The affected area is the back of the torso. This is a close-up image:
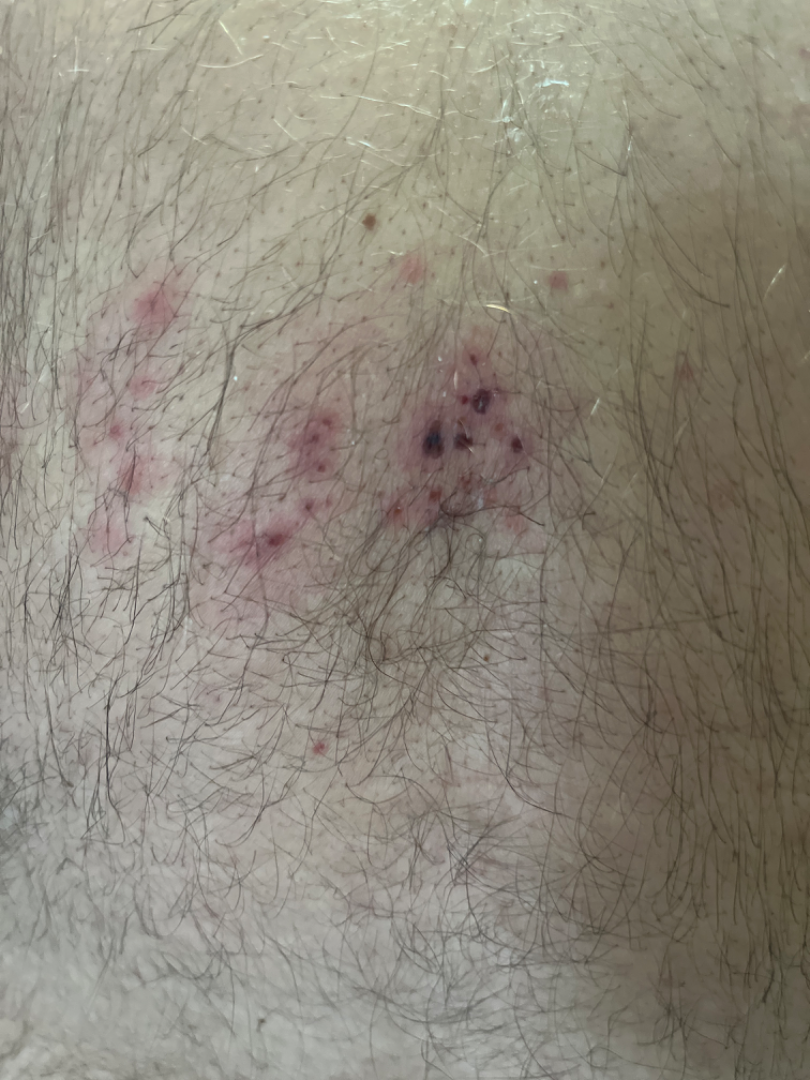Background:
The patient considered this a rash. The contributor reports the lesion is flat. The contributor reports bothersome appearance and itching.
Findings:
Reviewed remotely by one dermatologist: in keeping with Herpes Zoster.